A dermoscopy image of a single skin lesion, the patient is a male approximately 60 years of age:
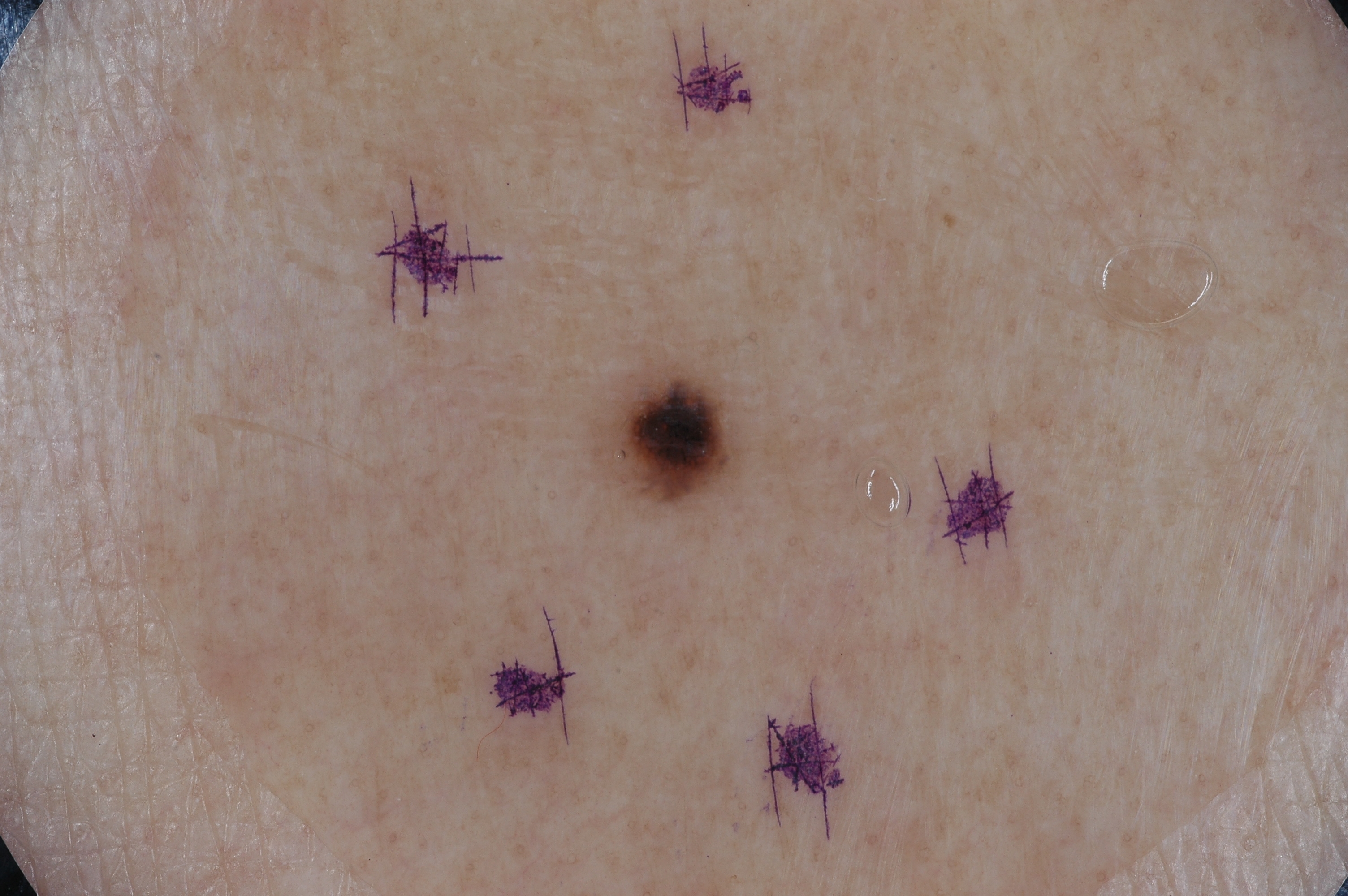{"dermoscopic_features": {"present": ["milia-like cysts", "pigment network"], "absent": ["negative network", "streaks"]}, "lesion_location": {"bbox_xyxy": [603, 363, 745, 511]}, "diagnosis": {"name": "melanocytic nevus", "malignancy": "benign", "lineage": "melanocytic", "provenance": "clinical"}}